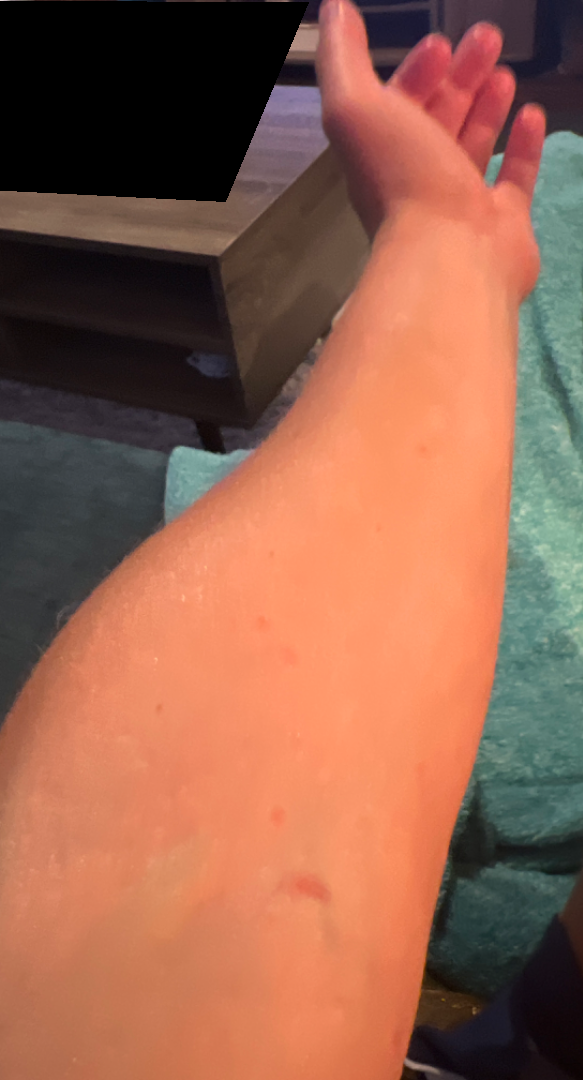Findings:
- assessment: indeterminate